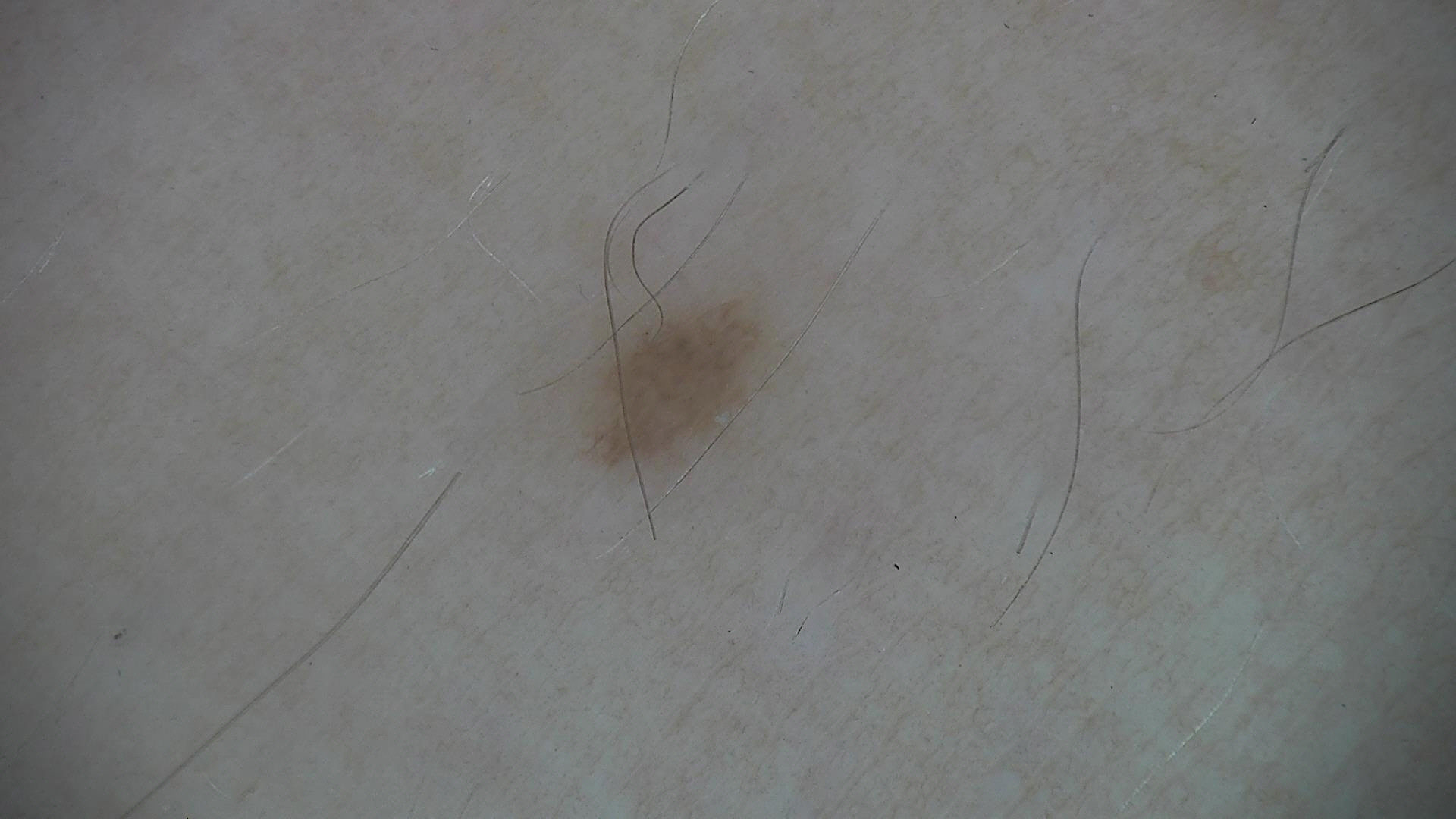A dermatoscopic image of a skin lesion.
Consistent with a benign lesion — a dysplastic junctional nevus.